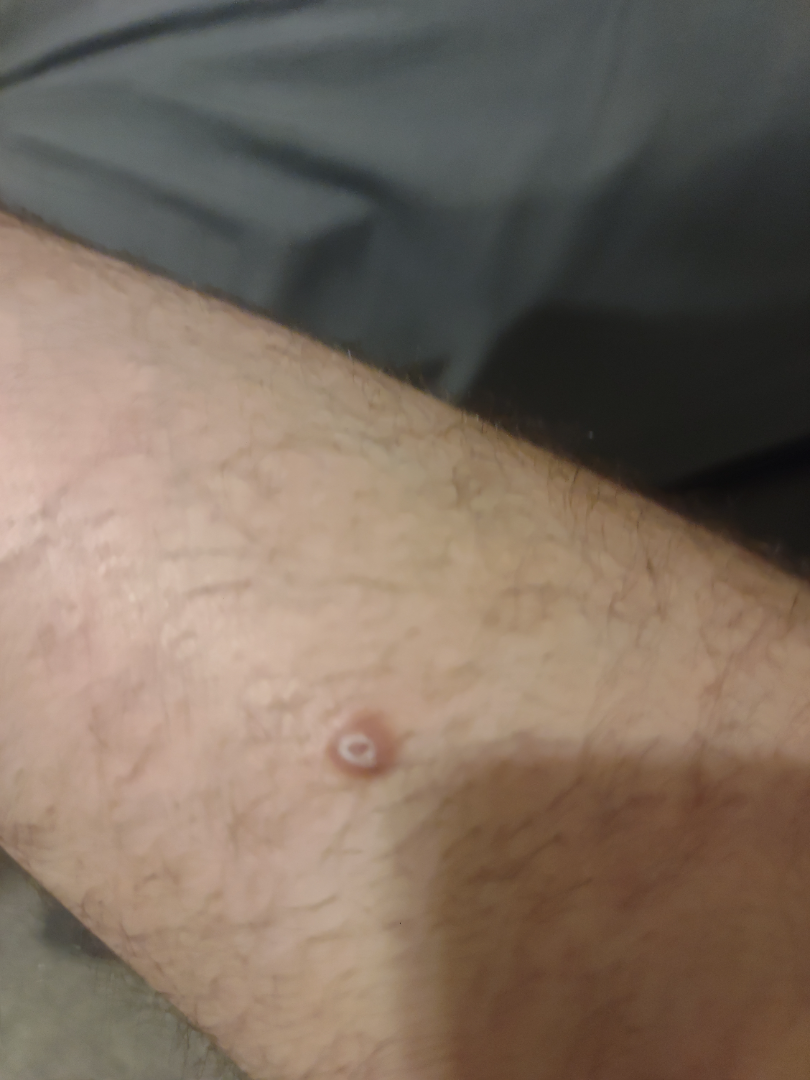differential diagnosis: Dermatofibroma, Cyst and Ingrown hair were each considered, in no particular order.